The referring clinician suspected seborrheic keratosis · the patient says their skin tans without first burning · a male subject age 64 · few moles overall by the patient's own estimate · a clinical photograph of a skin lesion.
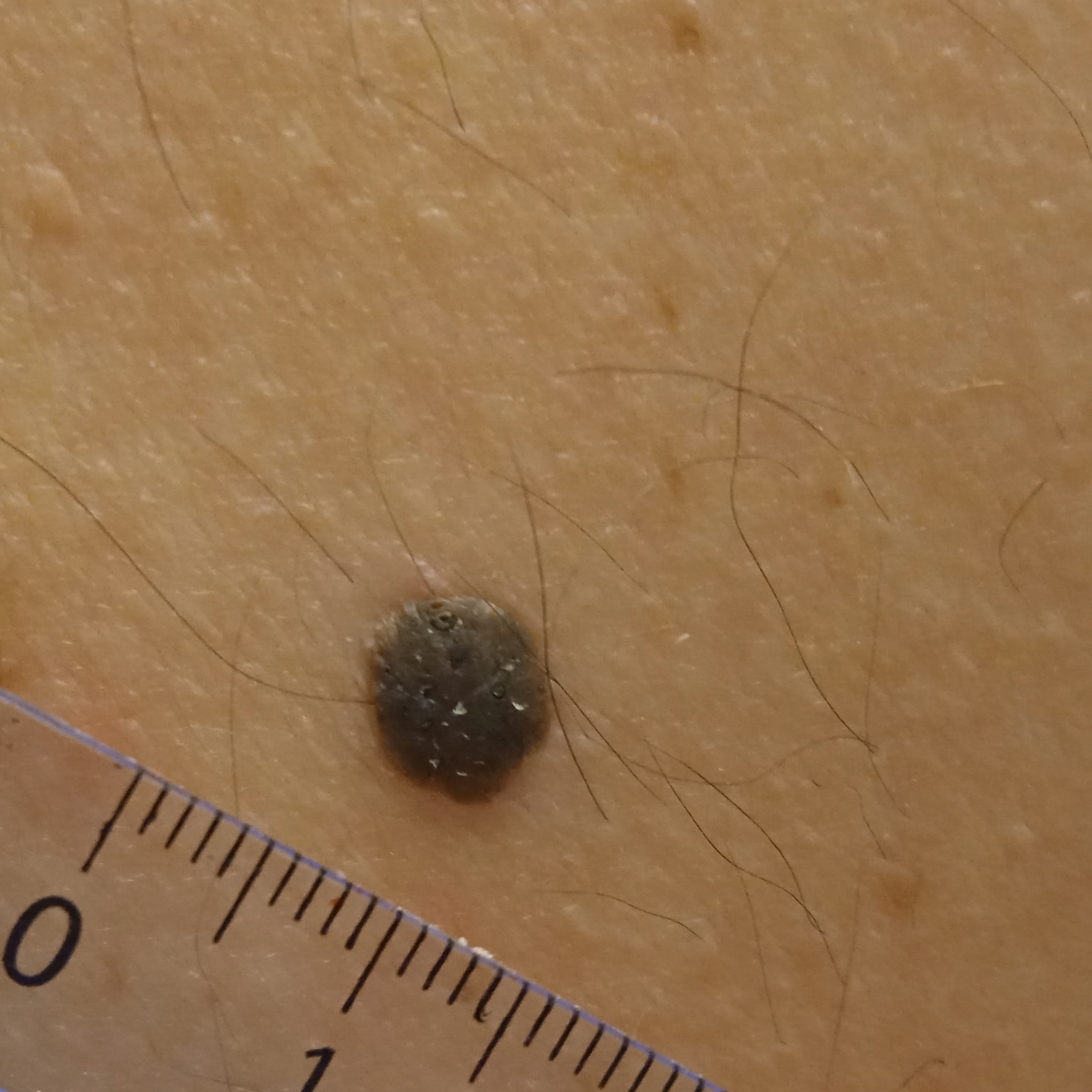<skin_lesion>
  <lesion_location>the back</lesion_location>
  <lesion_size>
    <diameter_mm>8.8</diameter_mm>
  </lesion_size>
  <diagnosis>
    <name>seborrheic keratosis</name>
    <malignancy>benign</malignancy>
  </diagnosis>
</skin_lesion>